A dermoscopic close-up of a skin lesion:
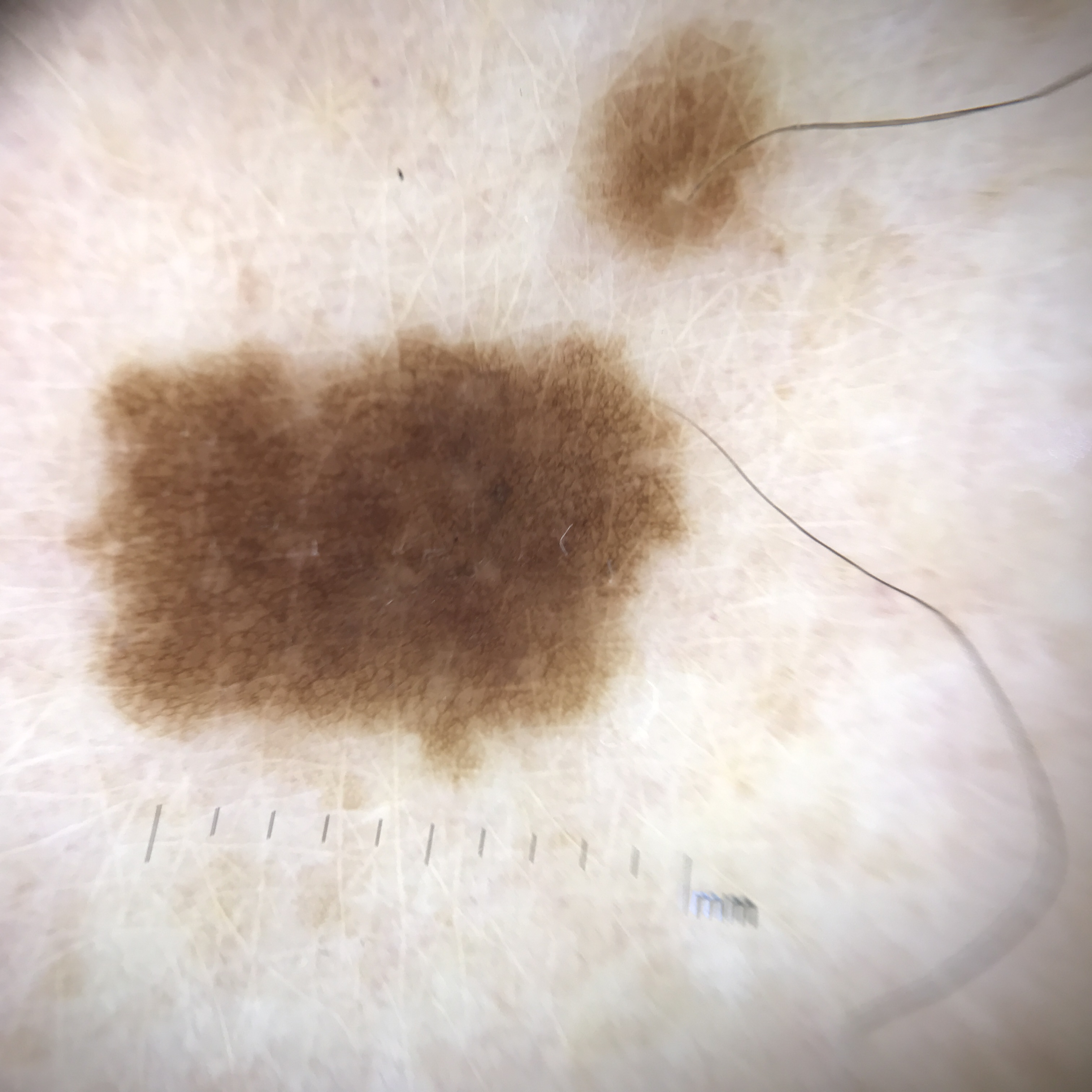Conclusion: Diagnosed as a dysplastic junctional nevus.